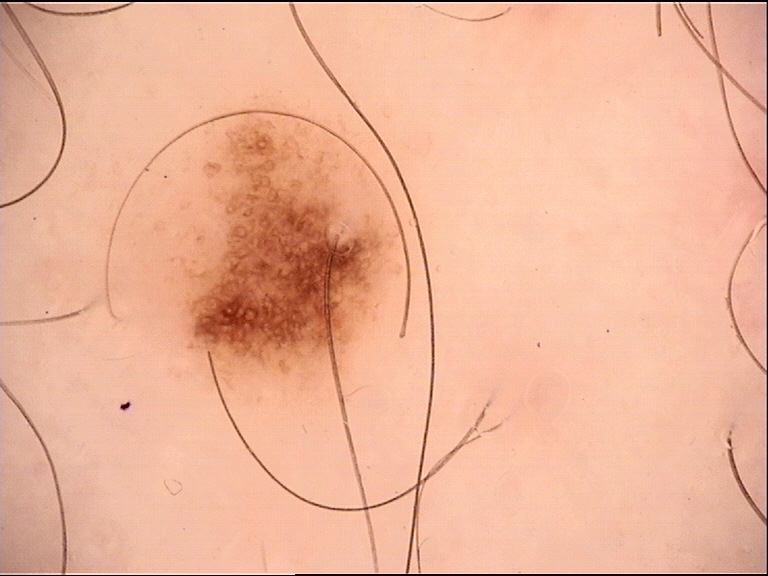Case:
A dermoscopic close-up of a skin lesion.
Impression:
Labeled as a dysplastic junctional nevus.